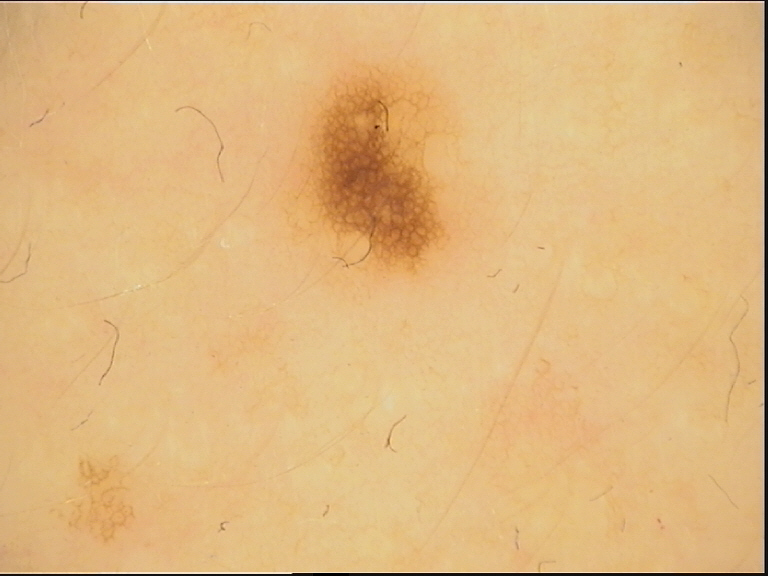A dermoscopic photograph of a skin lesion. This is a banal lesion. Classified as a junctional nevus.